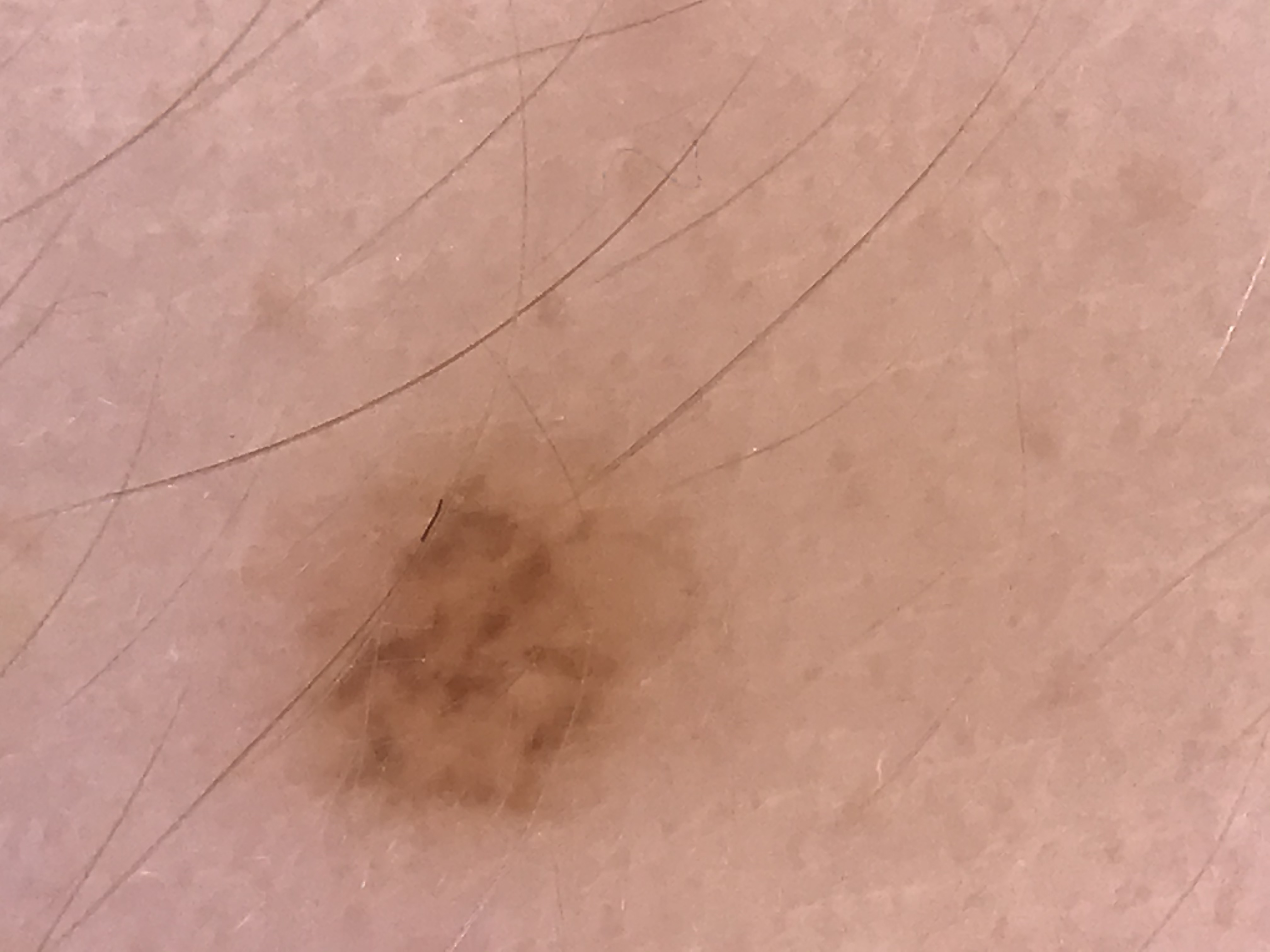Findings:
• diagnostic label: dysplastic compound nevus (expert consensus)